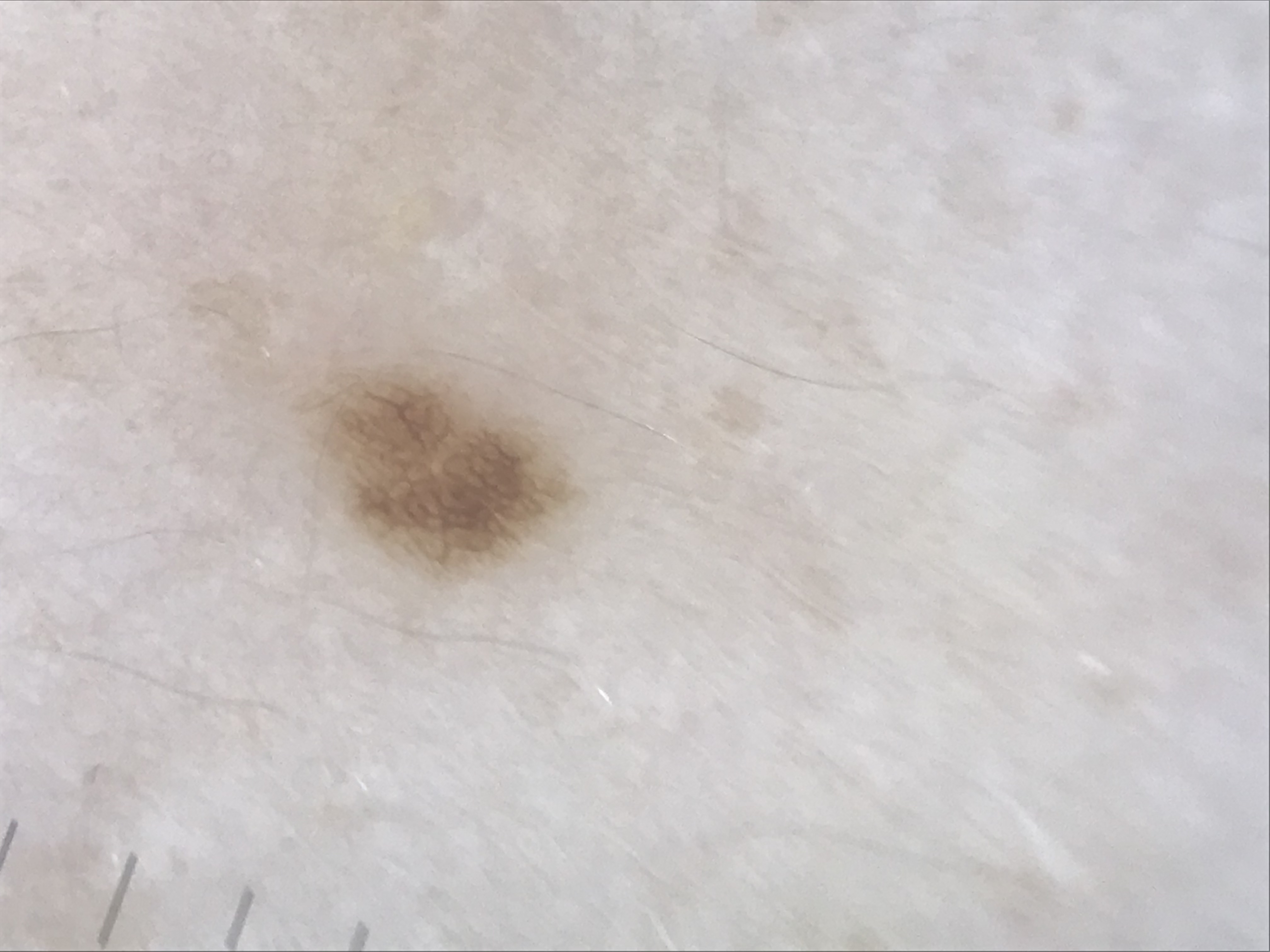Case:
* imaging: dermatoscopy
* diagnosis: junctional nevus (expert consensus)